An image taken at an angle.
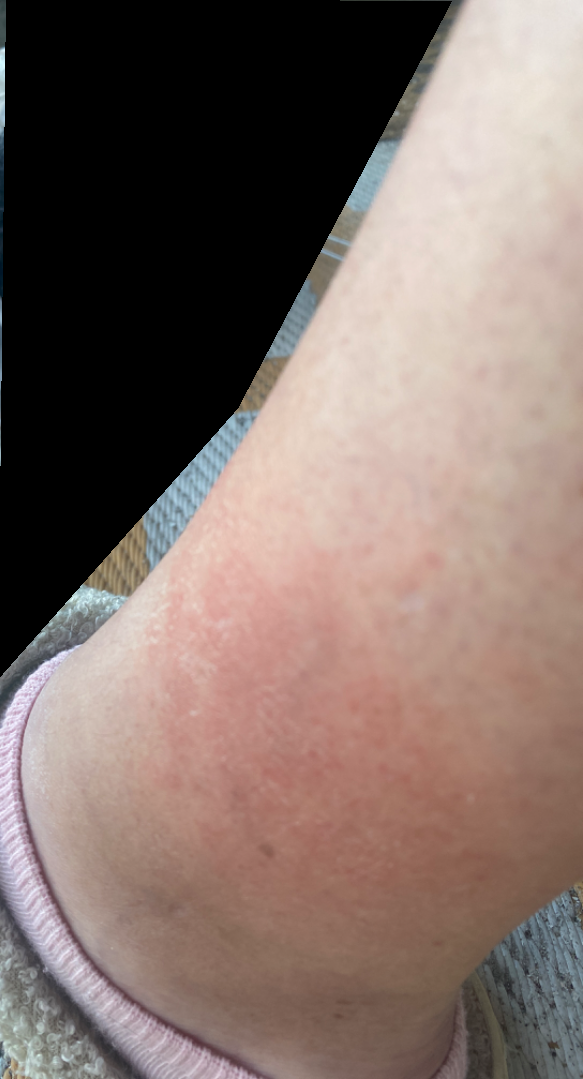On photographic review by a dermatologist, in keeping with Eczema.